A skin lesion imaged with a dermatoscope.
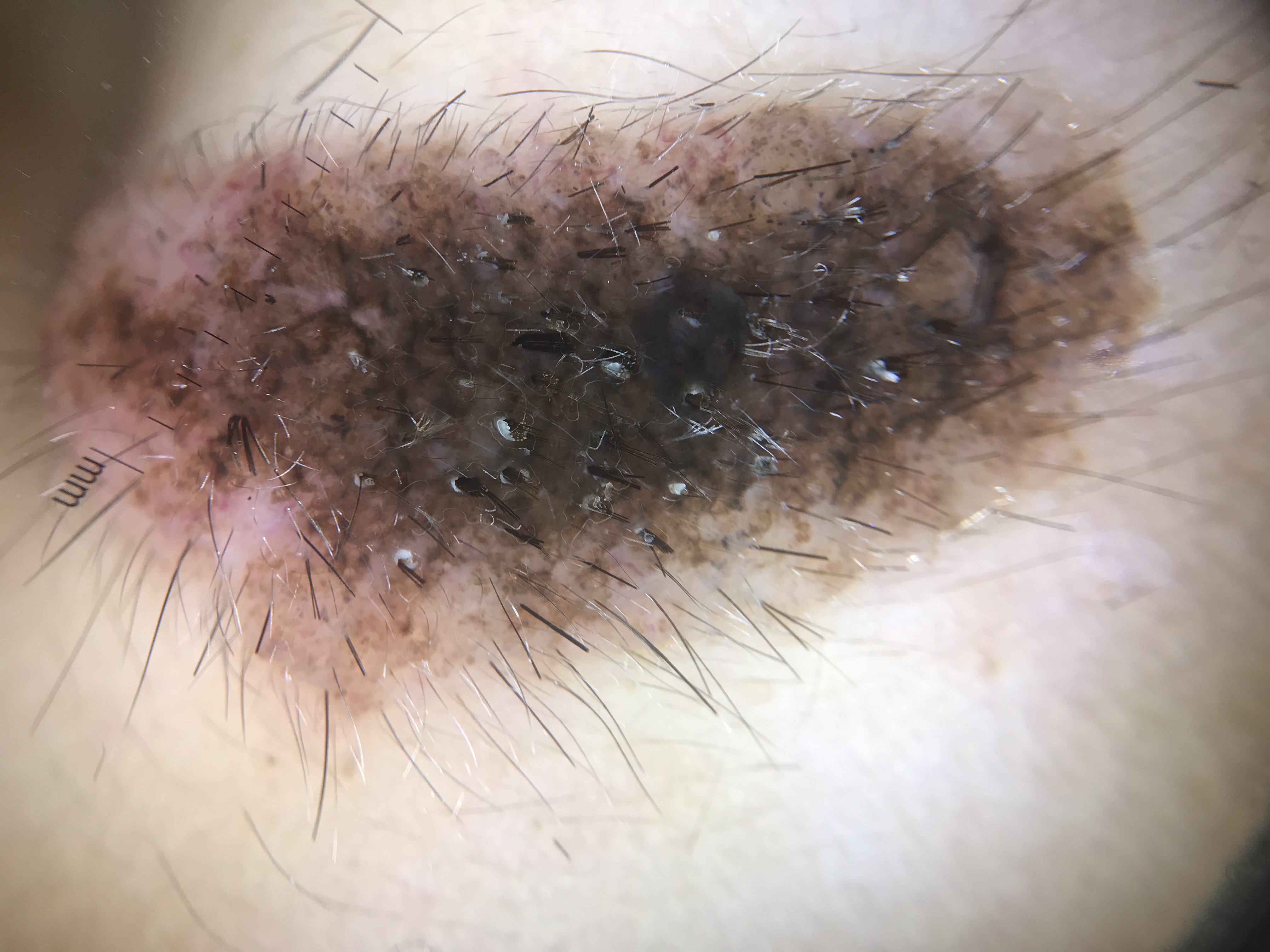The architecture is that of a banal lesion.
Classified as a congenital compound nevus.